The photograph was taken at an angle. Located on the leg. The subject is a male aged 30–39.
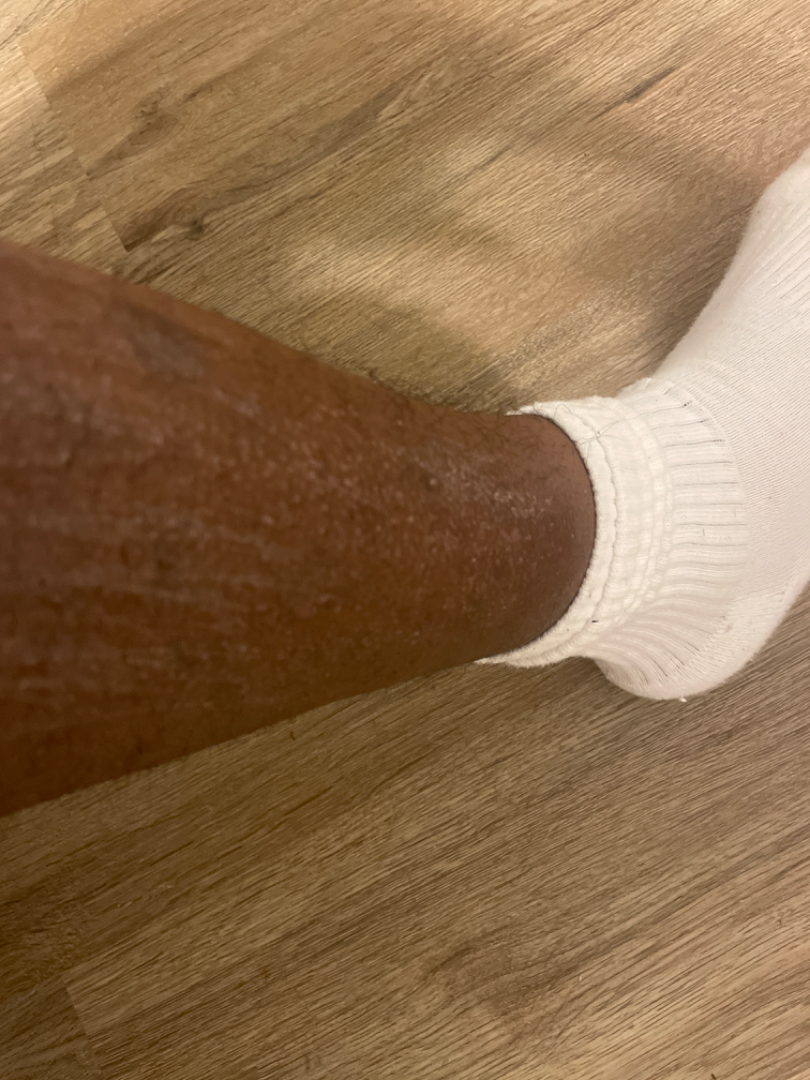Assessment: The condition could not be reliably identified from the image.